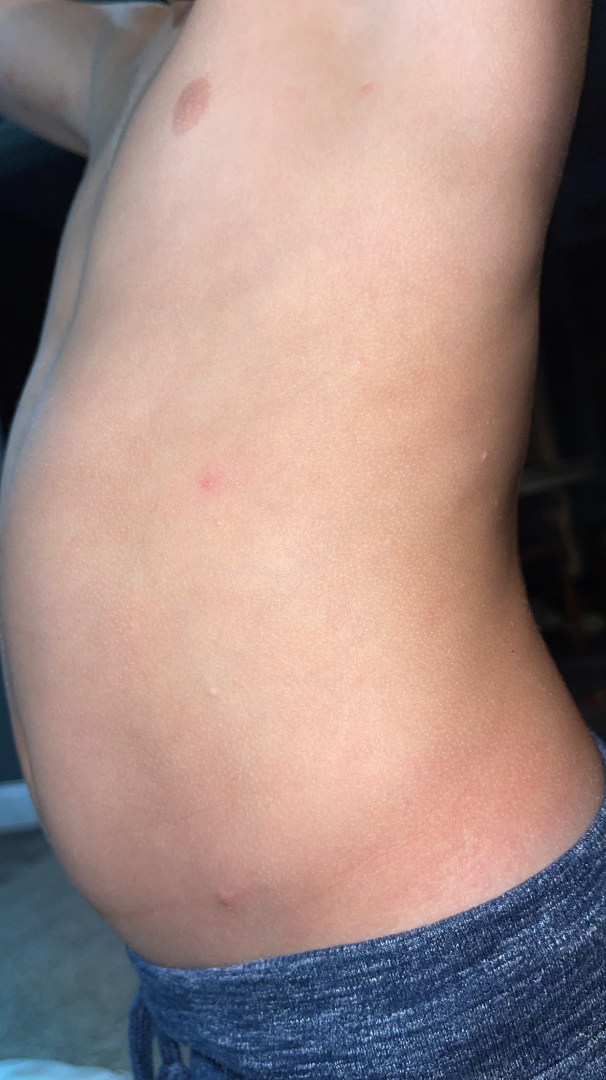The lesion involves the back of the torso and arm.
The photo was captured at an angle.
The reviewing clinician's impression was: favoring Molluscum Contagiosum; the differential also includes Folliculitis; an alternative is Papular acrodermatitis of childhood.